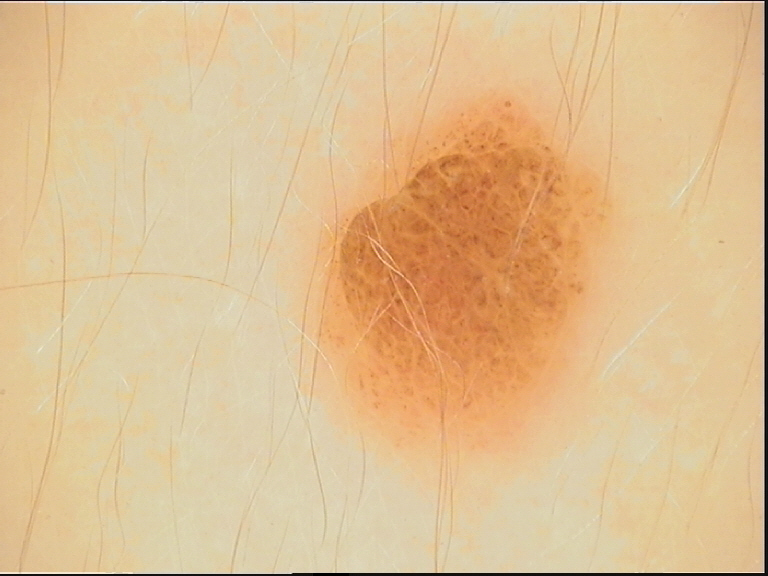The morphology is that of a banal lesion. Labeled as a compound nevus.